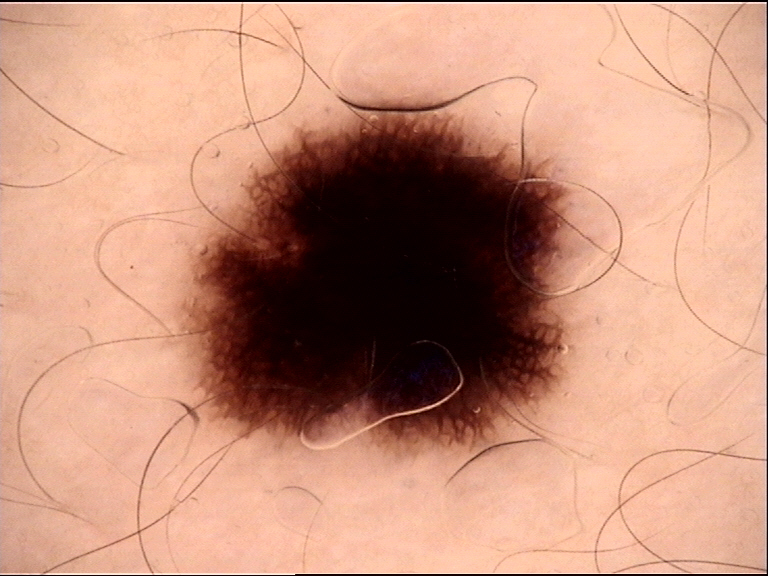Labeled as a benign lesion — a Spitz/Reed nevus.